A dermoscopic photograph of a skin lesion: 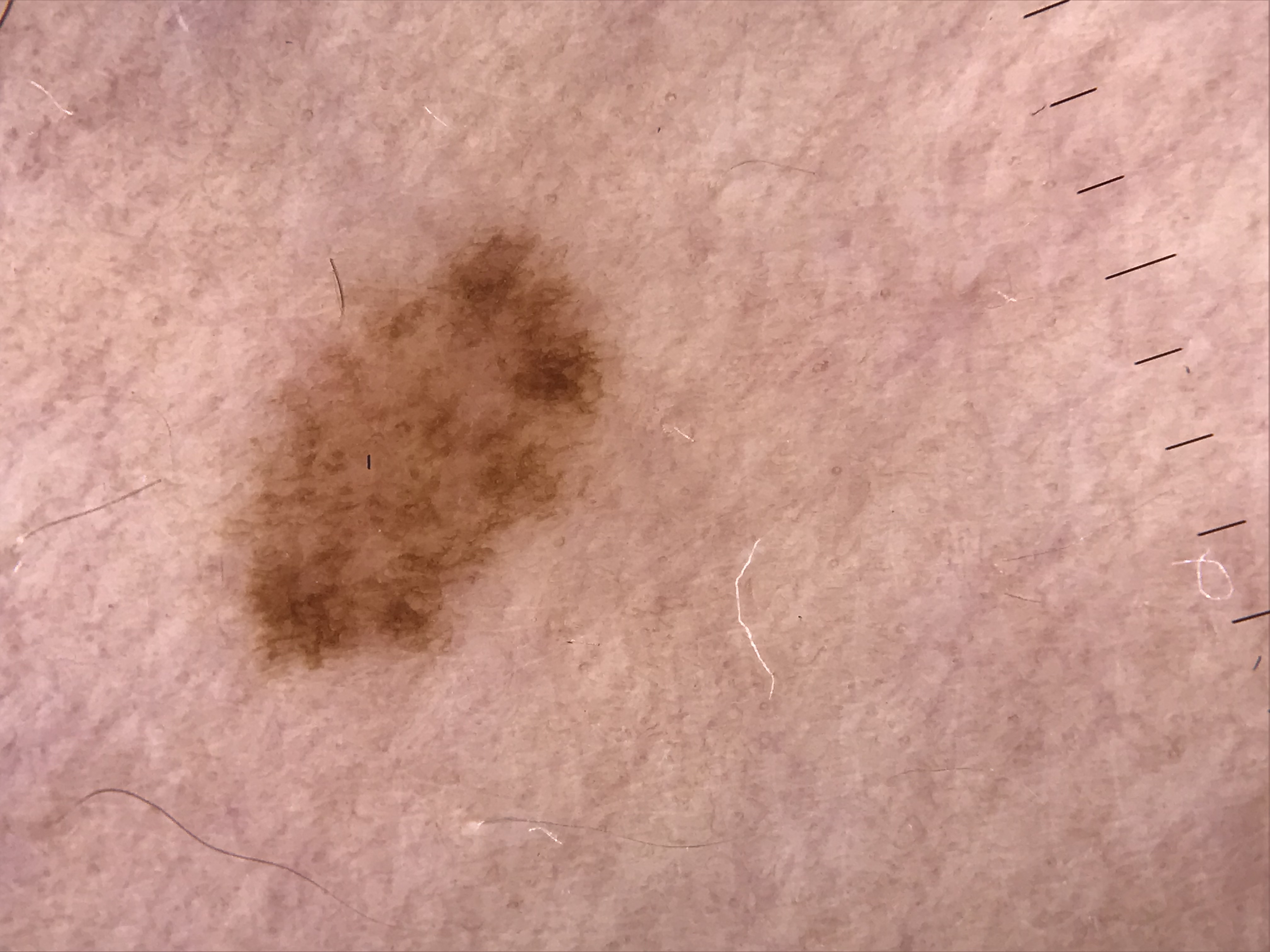<case>
<diagnosis>
<name>dysplastic junctional nevus</name>
<code>jd</code>
<malignancy>benign</malignancy>
<super_class>melanocytic</super_class>
<confirmation>expert consensus</confirmation>
</diagnosis>
</case>